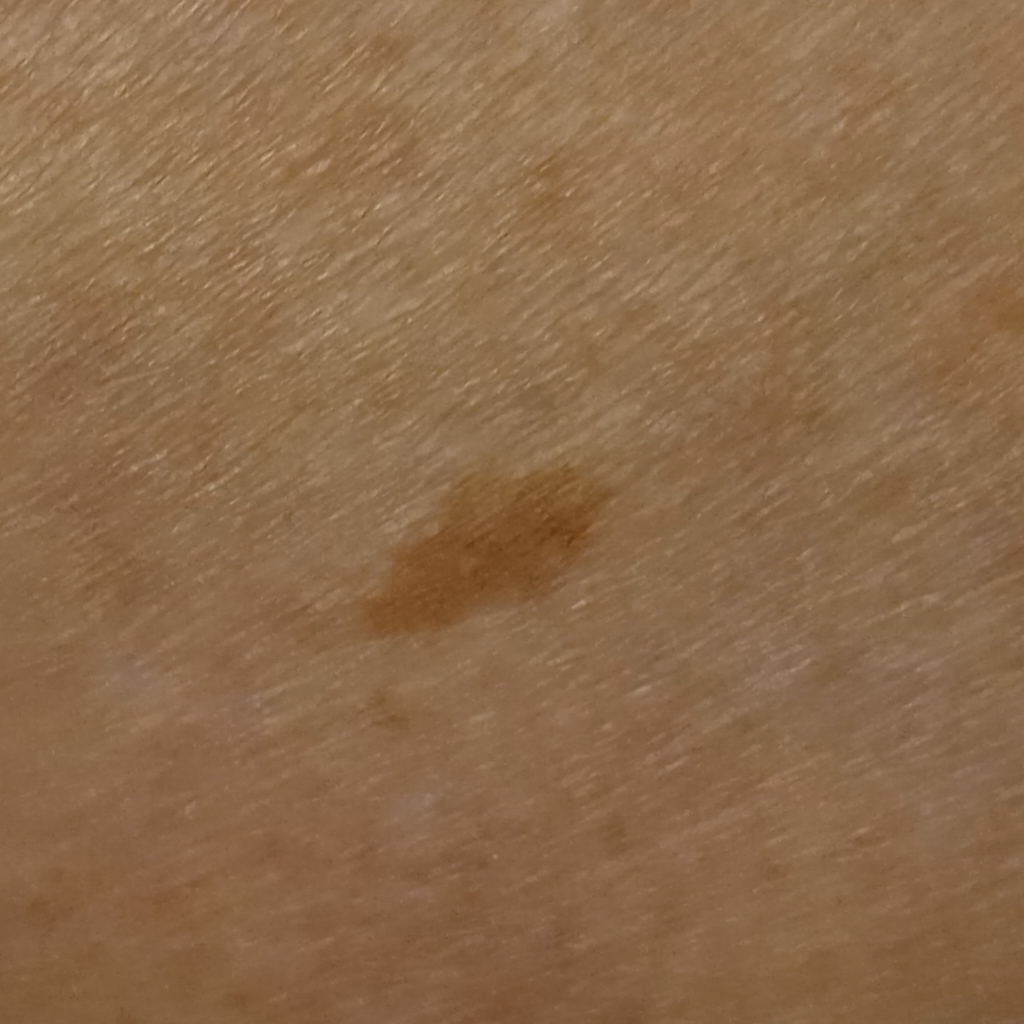| feature | finding |
|---|---|
| diagnosis | melanocytic nevus (dermatologist consensus) |